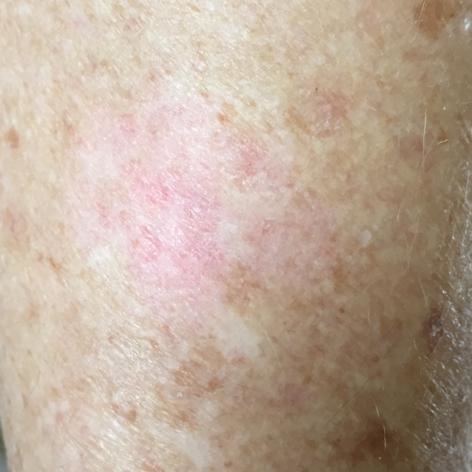Consistent with an actinic keratosis.